A dermoscopic photograph of a skin lesion:
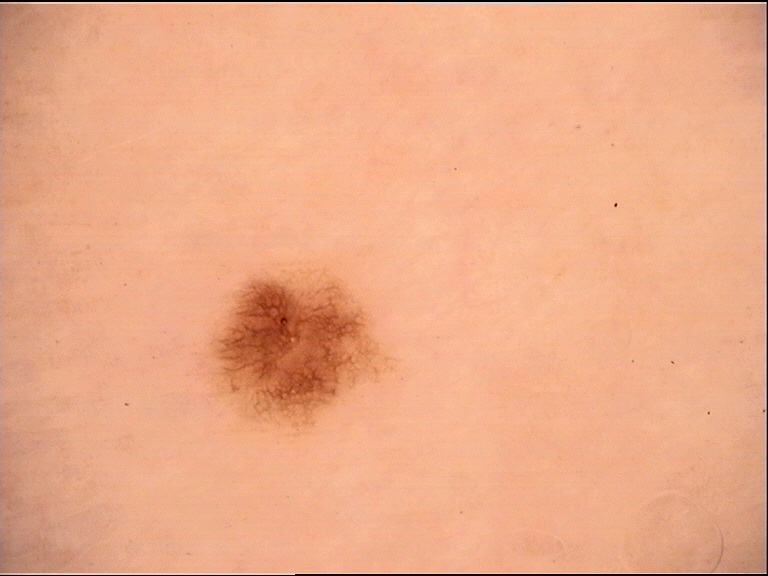Classified as a benign lesion — a dysplastic junctional nevus.